A dermoscopic close-up of a skin lesion: 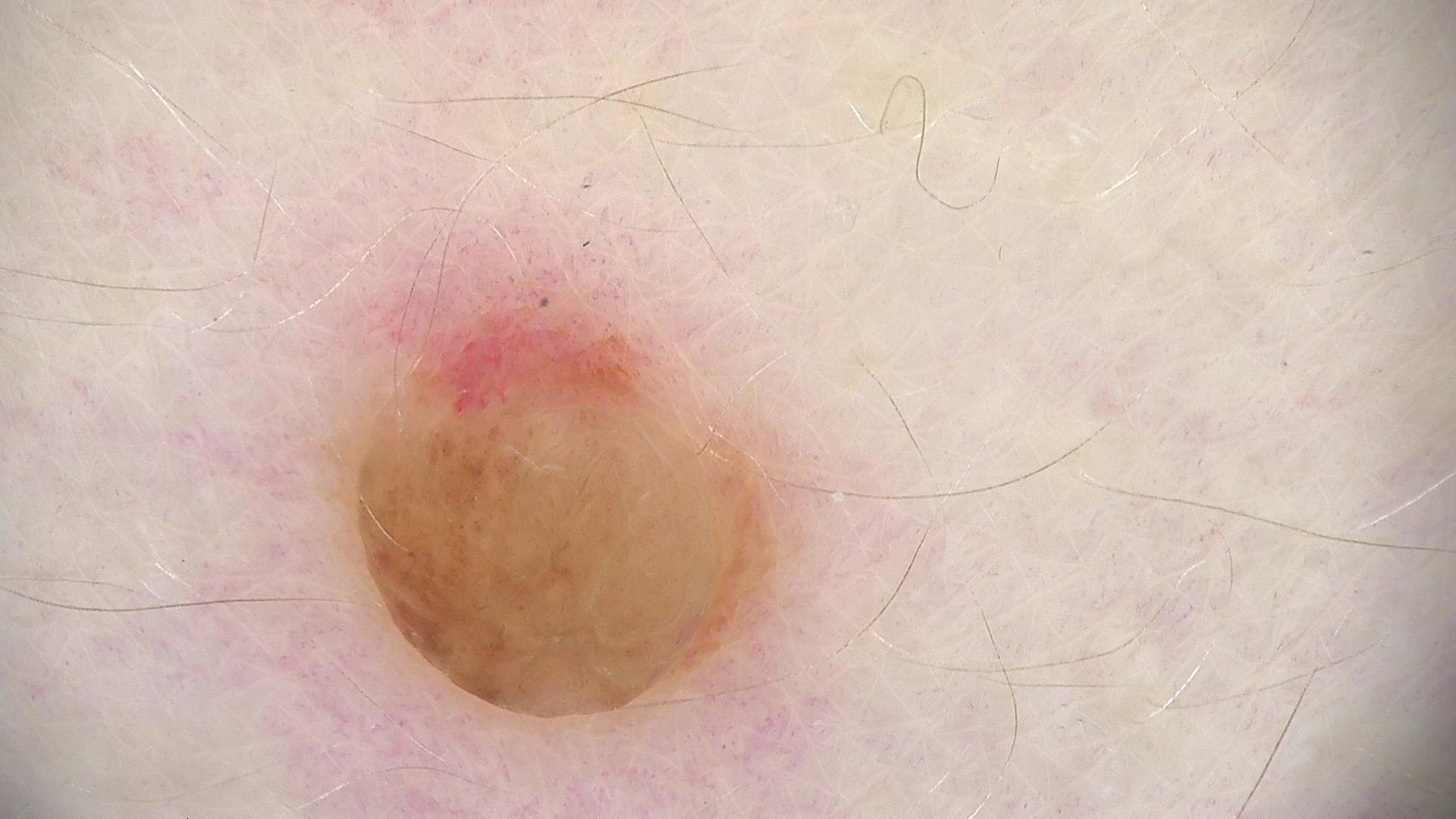| field | value |
|---|---|
| classification | banal |
| label | dermal nevus (expert consensus) |